A dermoscopy image of a single skin lesion: 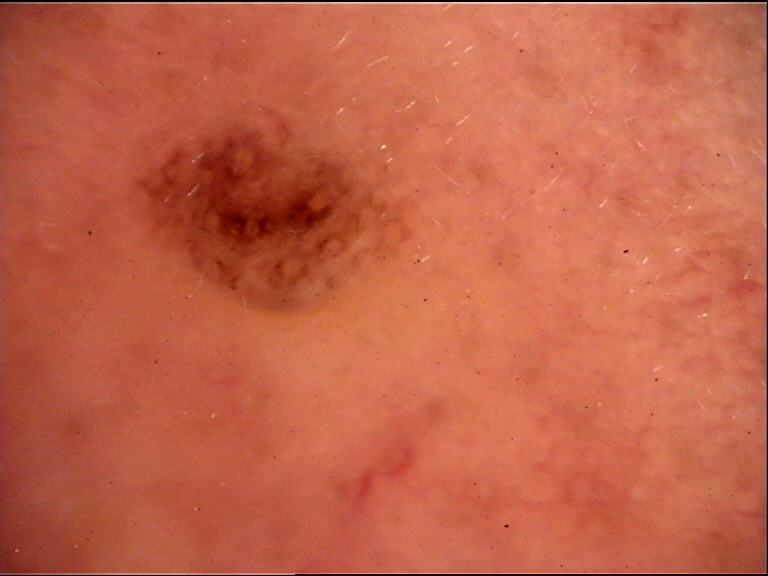Consistent with a Miescher nevus.